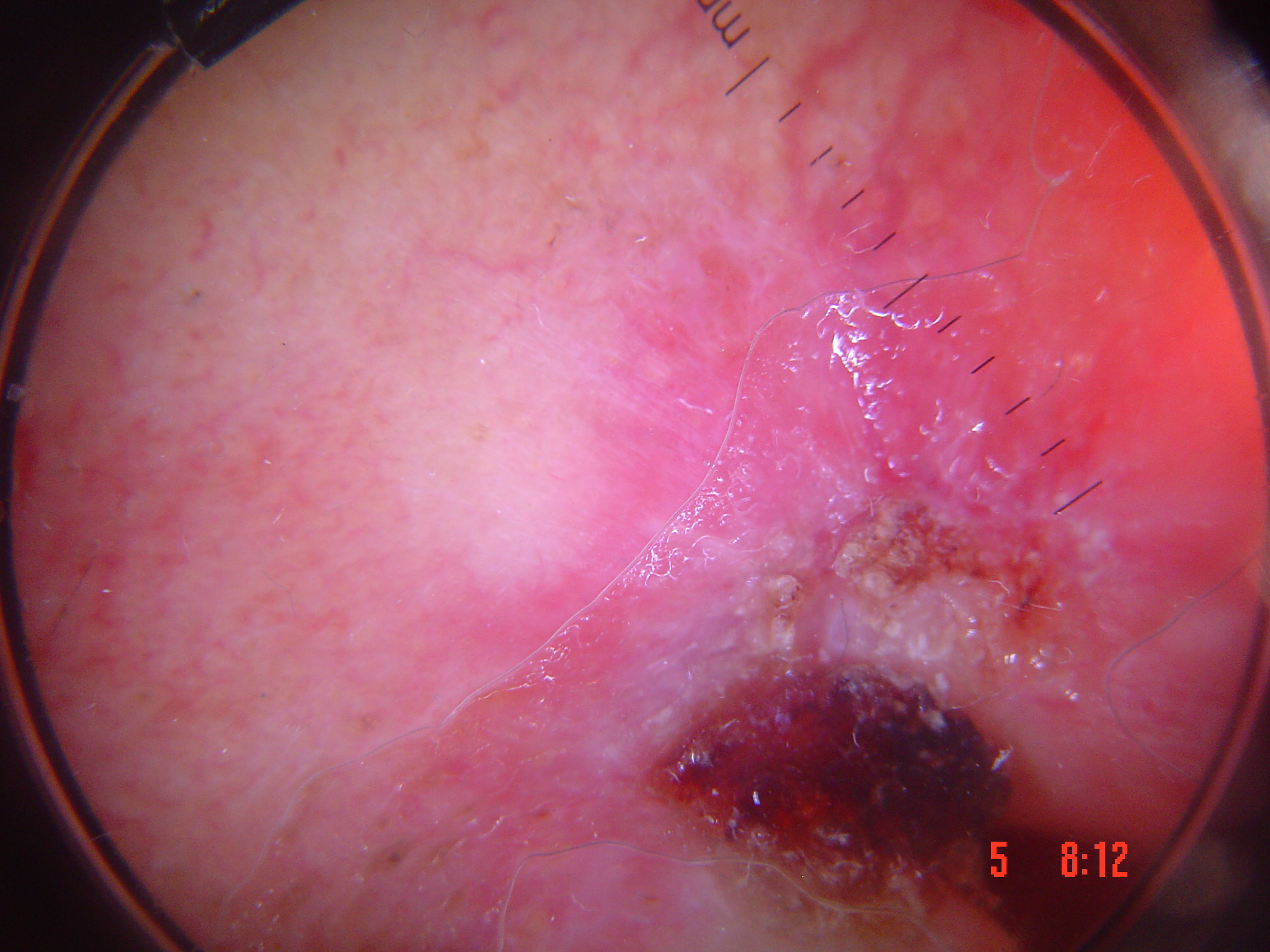Summary:
The morphology is that of a keratinocytic lesion.
Conclusion:
Confirmed on histopathology as a skin cancer — a basal cell carcinoma.